Dermoscopy of a skin lesion · the subject is a male approximately 30 years of age.
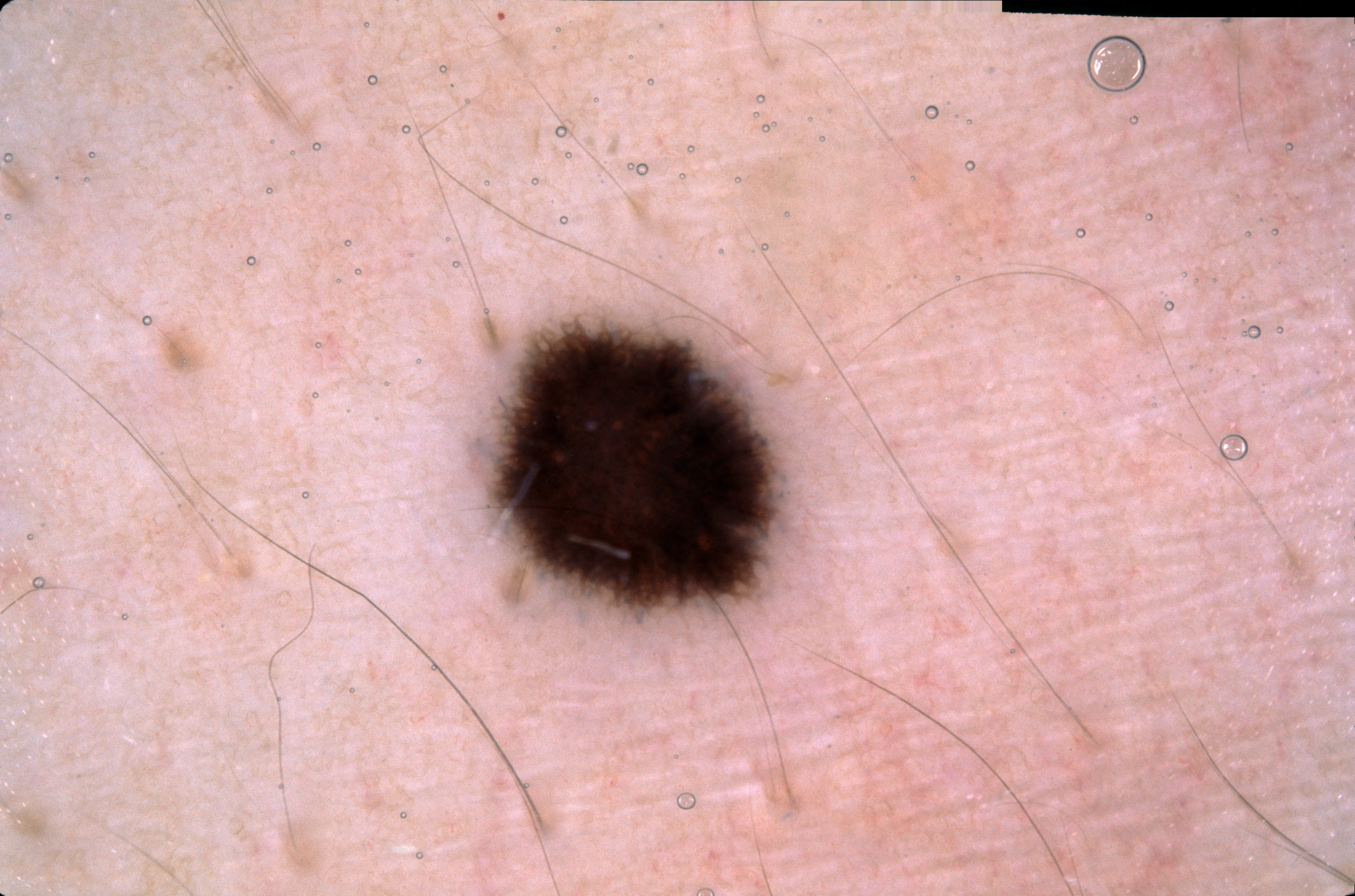dermoscopic_features:
  present:
    - pigment network
  absent:
    - negative network
    - streaks
    - milia-like cysts
lesion_location:
  bbox_xyxy:
    - 498
    - 322
    - 783
    - 616
lesion_extent:
  approx_field_fraction_pct: 5
diagnosis:
  name: melanocytic nevus
  malignancy: benign
  lineage: melanocytic
  provenance: clinical